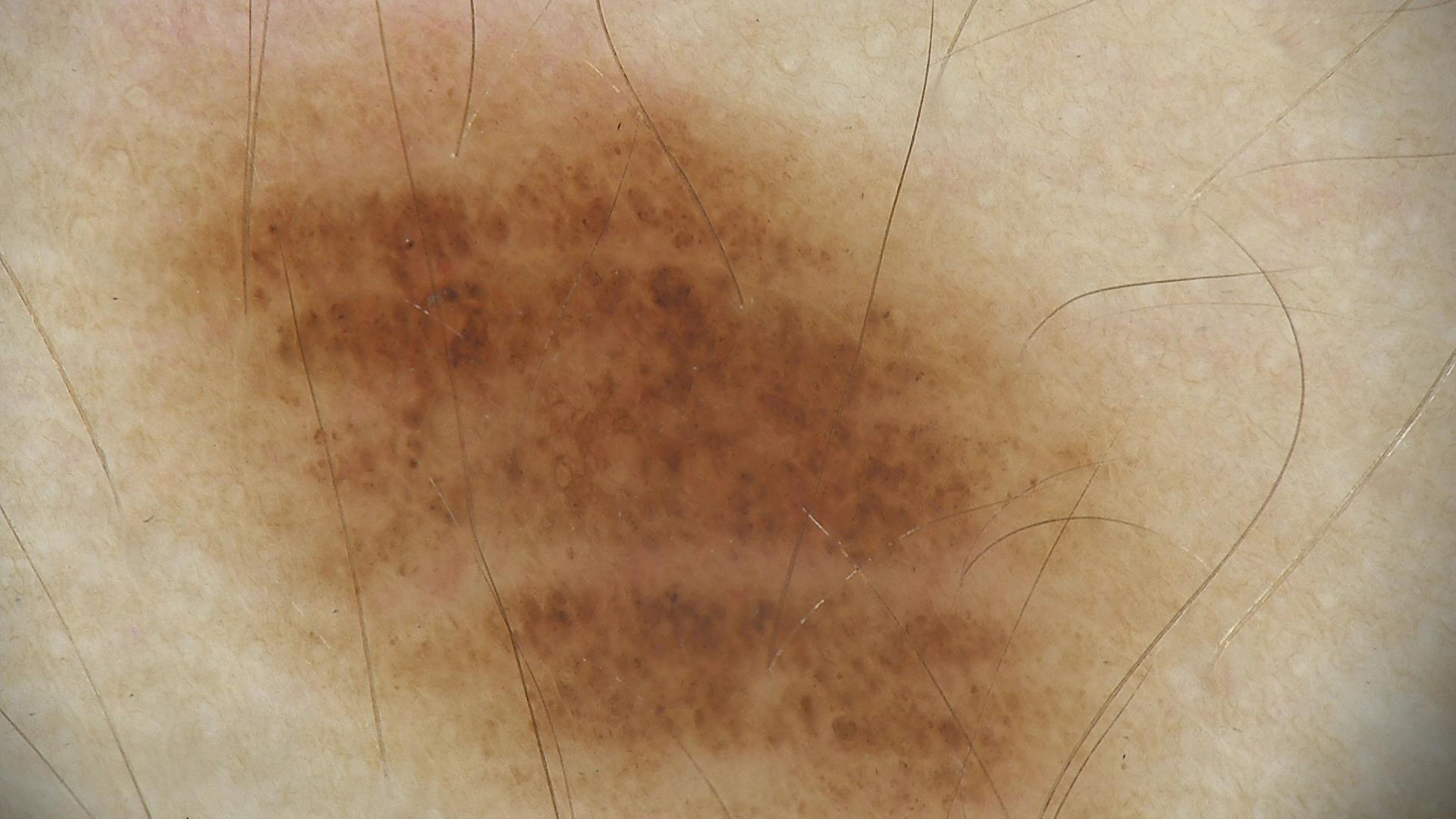Findings:
A dermatoscopic image of a skin lesion.
Conclusion:
The diagnosis was a dysplastic junctional nevus.